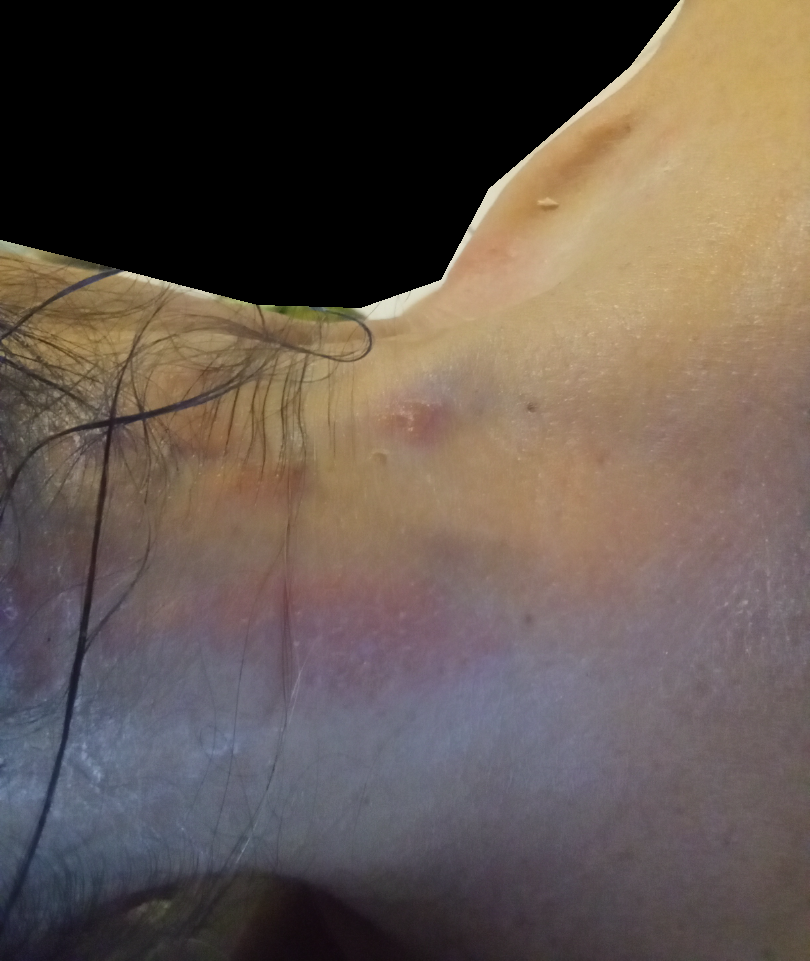| key | value |
|---|---|
| assessment | indeterminate |
| body site | head or neck |
| contributor | female, age 50–59 |
| view | at an angle |